Acquired for a research image collection, with no referral diagnosis · few moles overall by the patient's own estimate.
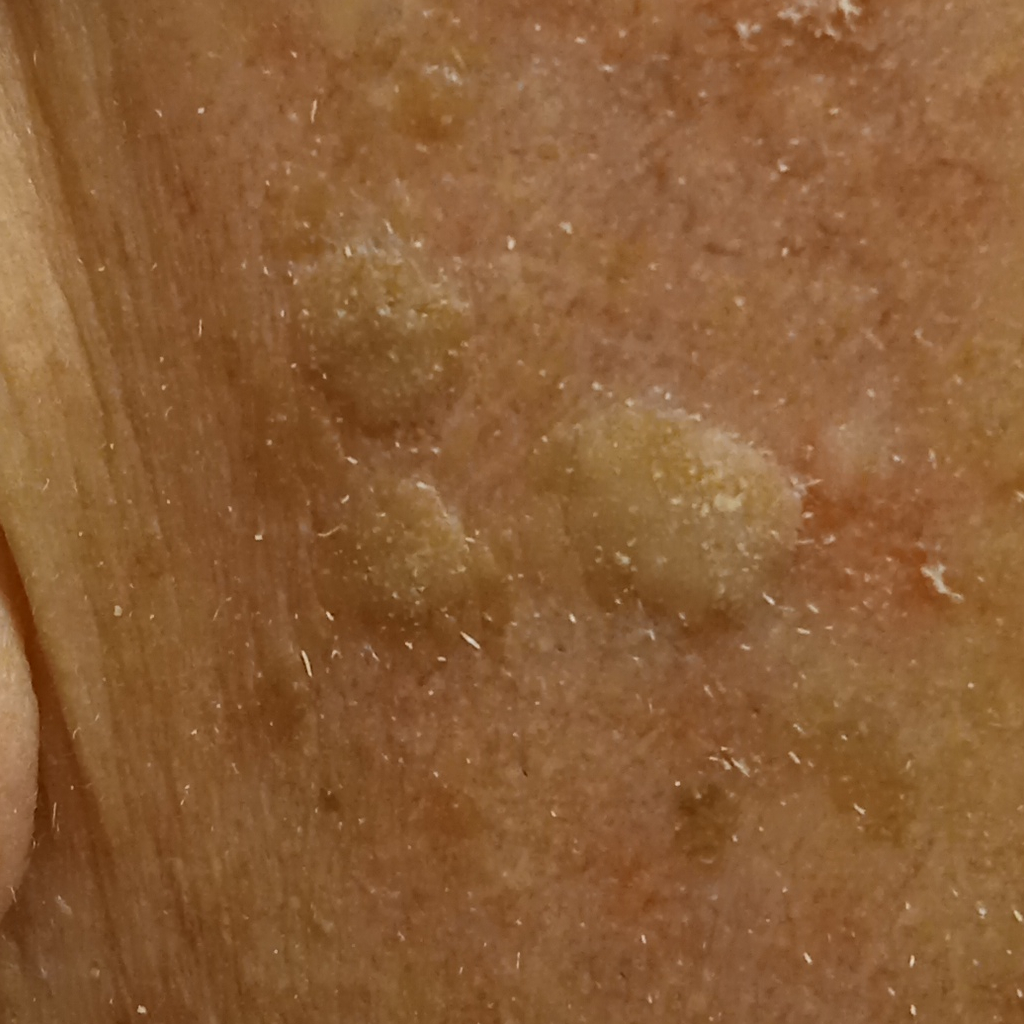The lesion is located on the face. The lesion measures approximately 7.5 mm. The lesion was assessed as a seborrheic keratosis.